A female subject 56 years old. A clinical photo of a skin lesion taken with a smartphone. Recorded as skin type II. The chart records prior skin cancer (patient or family), no alcohol use, and no tobacco use — 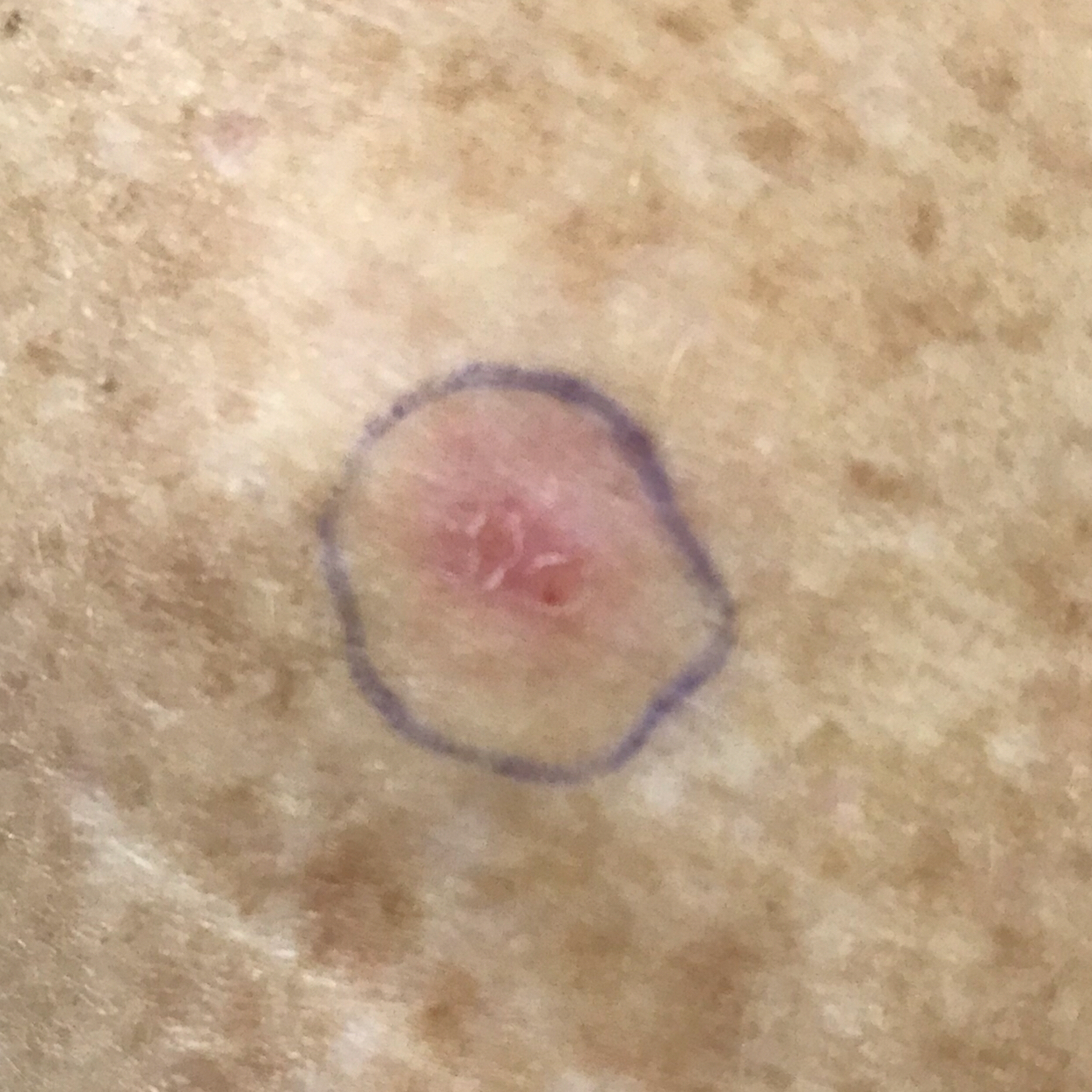Findings: The lesion was found on an arm. The lesion measures 7 × 6 mm. Per patient report, the lesion itches and has bled. Conclusion: Histopathology confirmed a basal cell carcinoma.